An image taken at an angle.
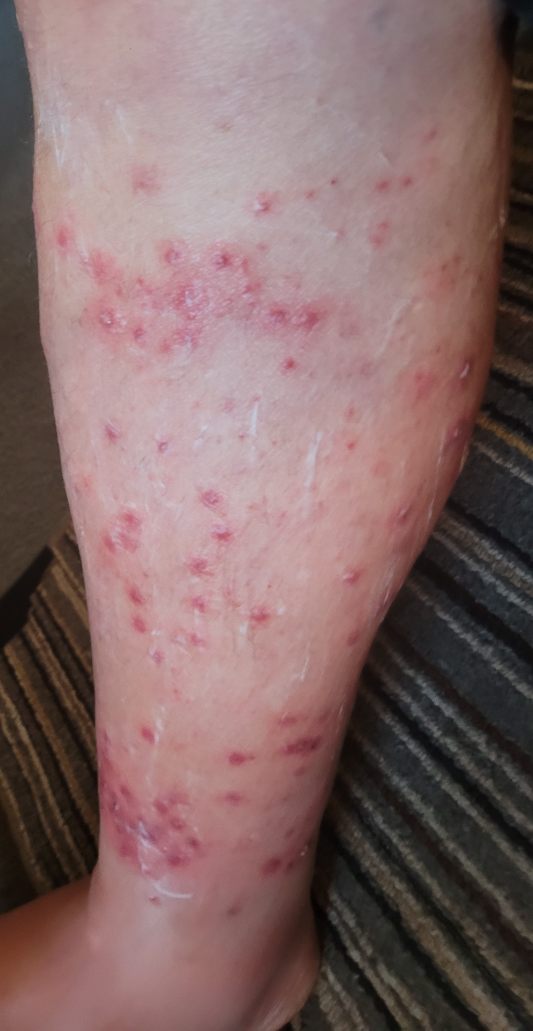differential diagnosis = one reviewing dermatologist: the impression on review was Insect Bite.